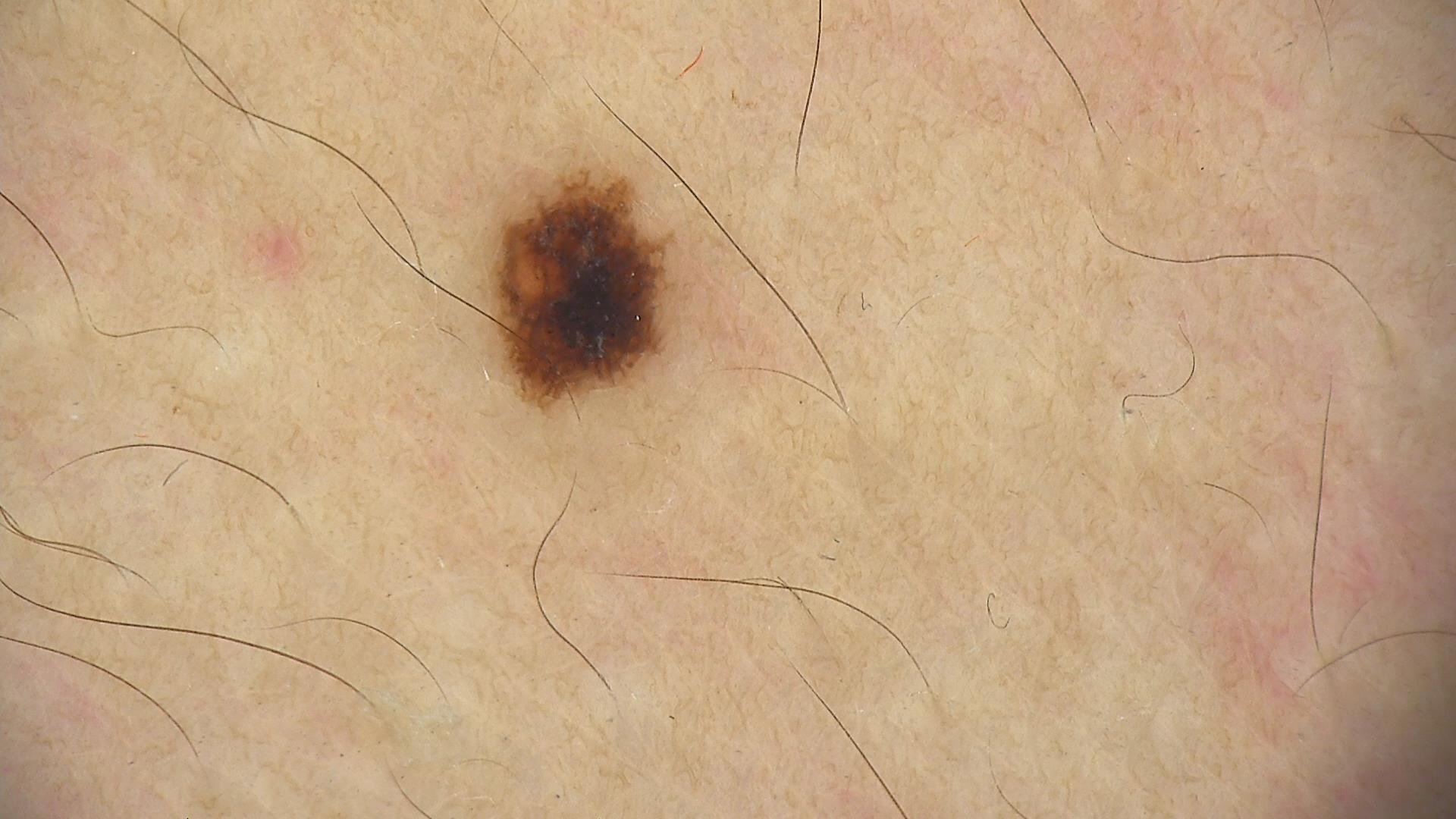assessment = dysplastic junctional nevus (expert consensus).